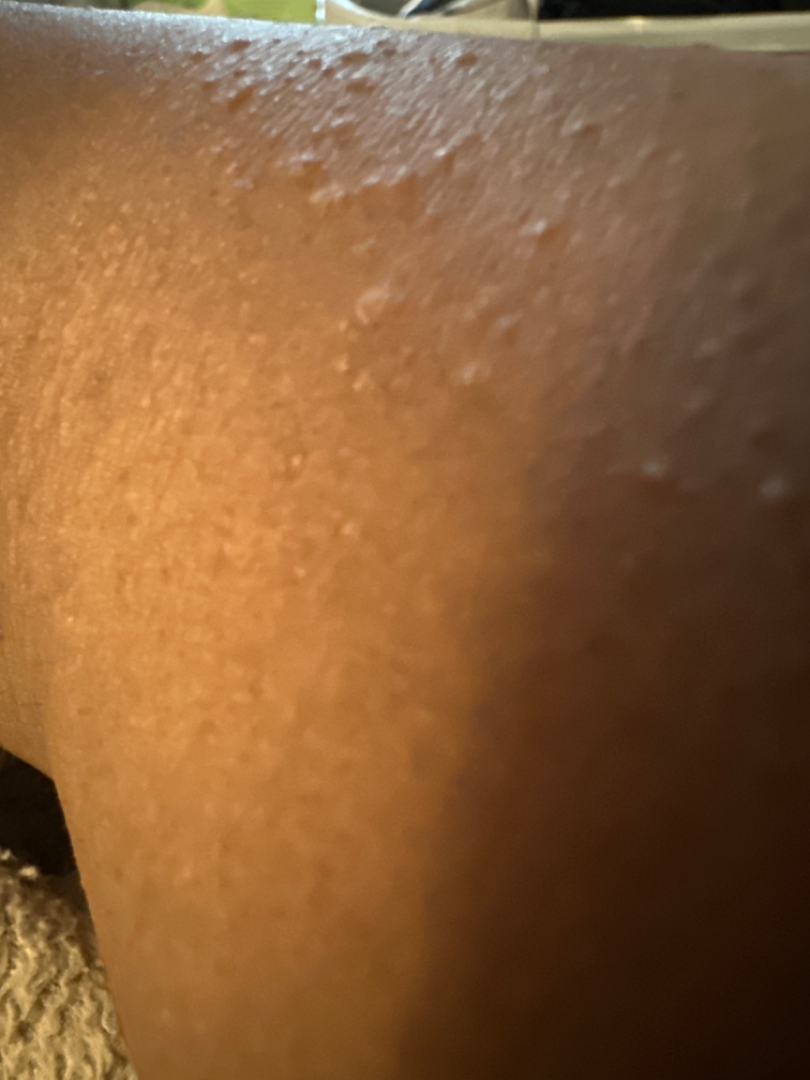The patient reported no systemic symptoms.
The lesion is described as fluid-filled.
The photograph was taken at an angle.
Female subject, age 18–29.
The lesion involves the arm.
Symptoms reported: itching, bothersome appearance, enlargement and burning.
The contributor notes the condition has been present for one to four weeks.
On remote dermatologist review, the differential includes Eczema and Lichen nitidus, with no clear leading consideration; less probable is Milia; less likely is Hypersensitivity.